A skin lesion imaged with a dermatoscope.
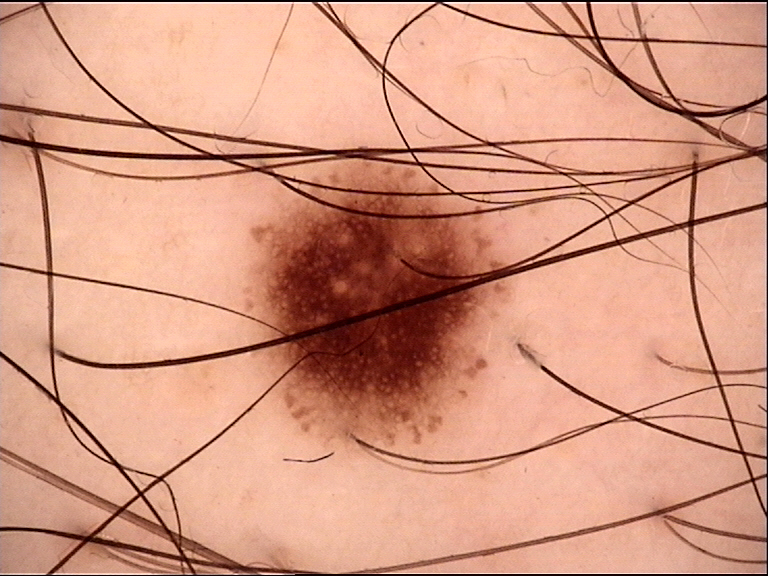Impression: Diagnosed as a benign lesion — a dysplastic junctional nevus.